A dermoscopy image of a single skin lesion: 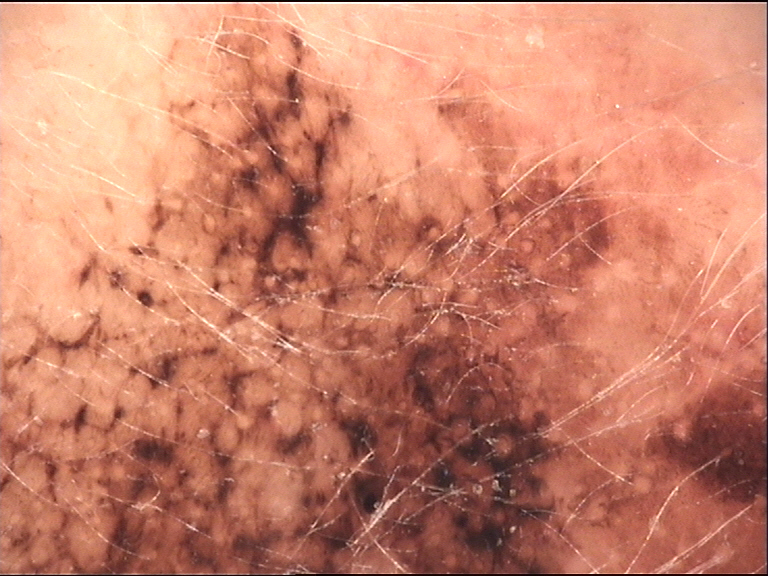Histopathologically confirmed as a lentigo maligna.